The photograph is a close-up of the affected area; skin tone: lay reviewers estimated Monk Skin Tone 3–4.
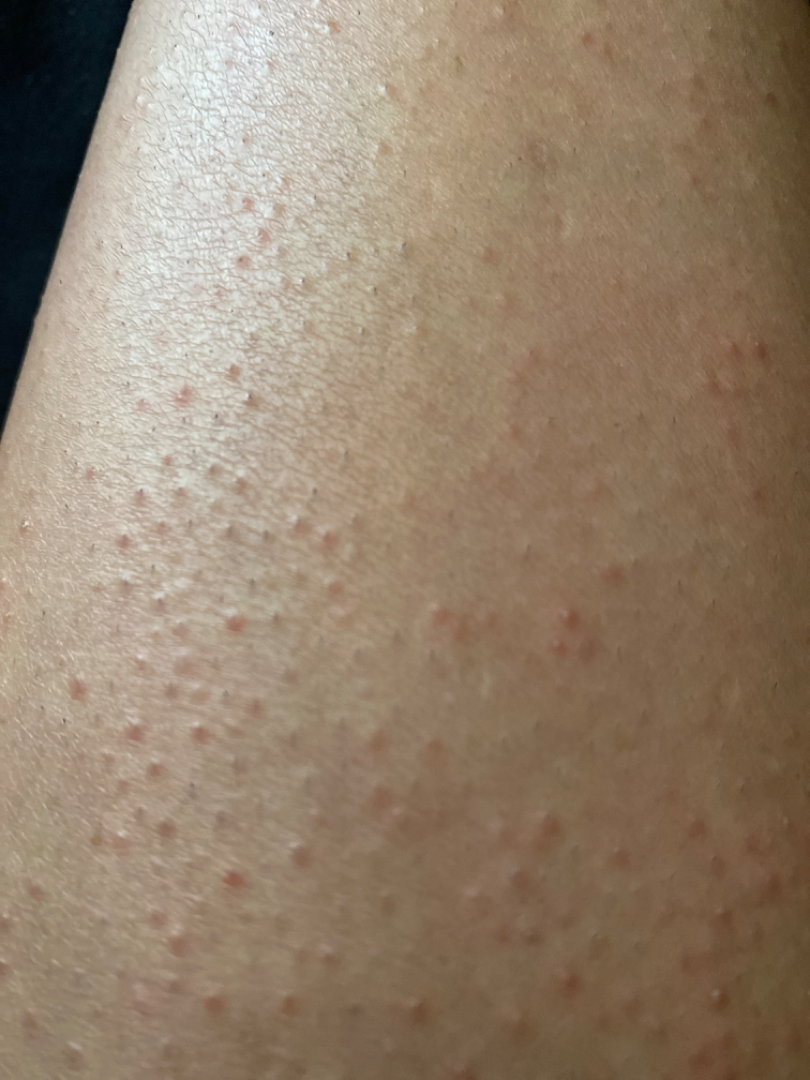| key | value |
|---|---|
| differential | the favored diagnosis is Lichen nitidus; also consider Lichen planus/lichenoid eruption; an alternative is Molluscum Contagiosum |